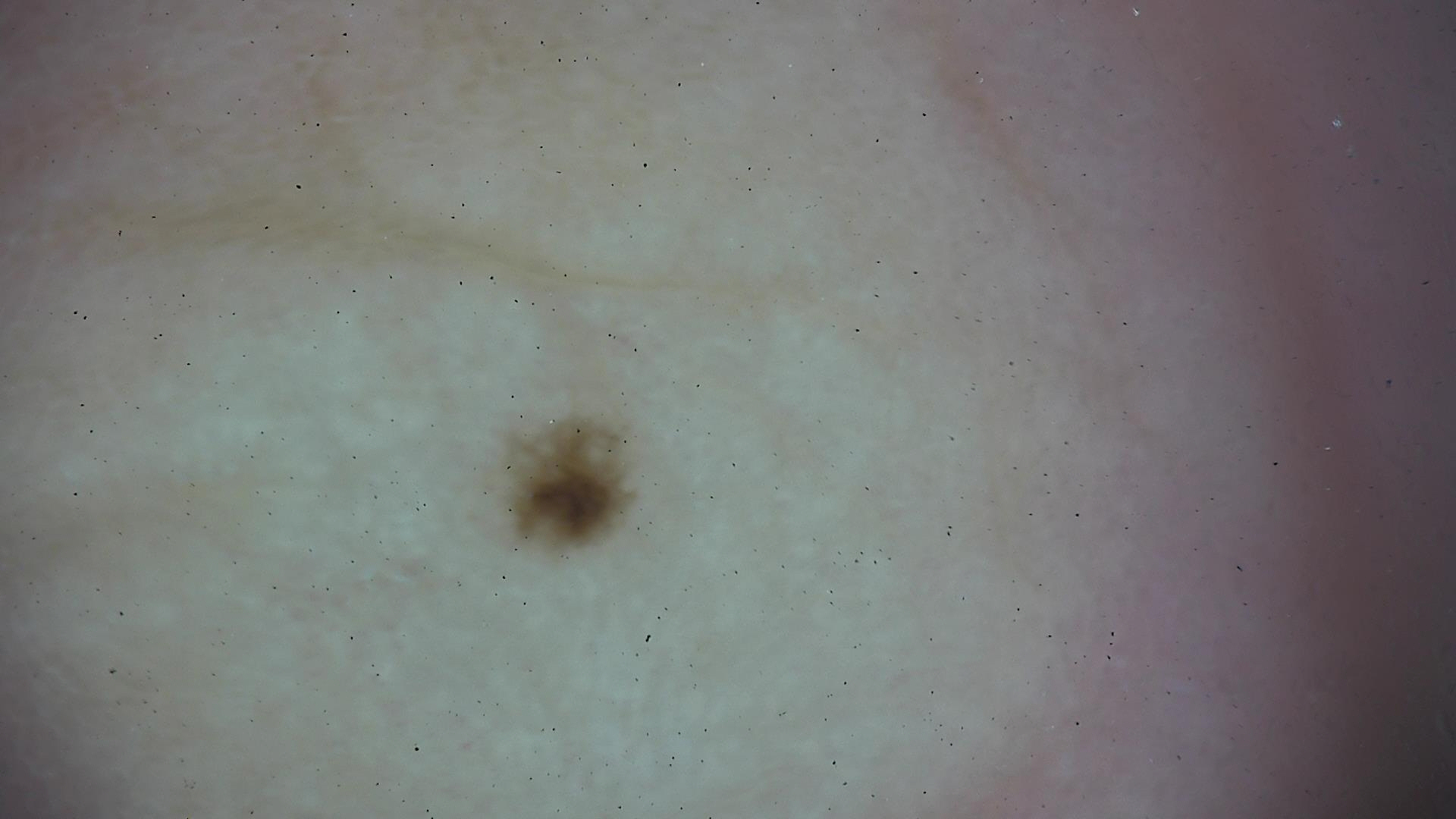Findings: A dermatoscopic image of a skin lesion. Impression: Labeled as an acral dysplastic junctional nevus.